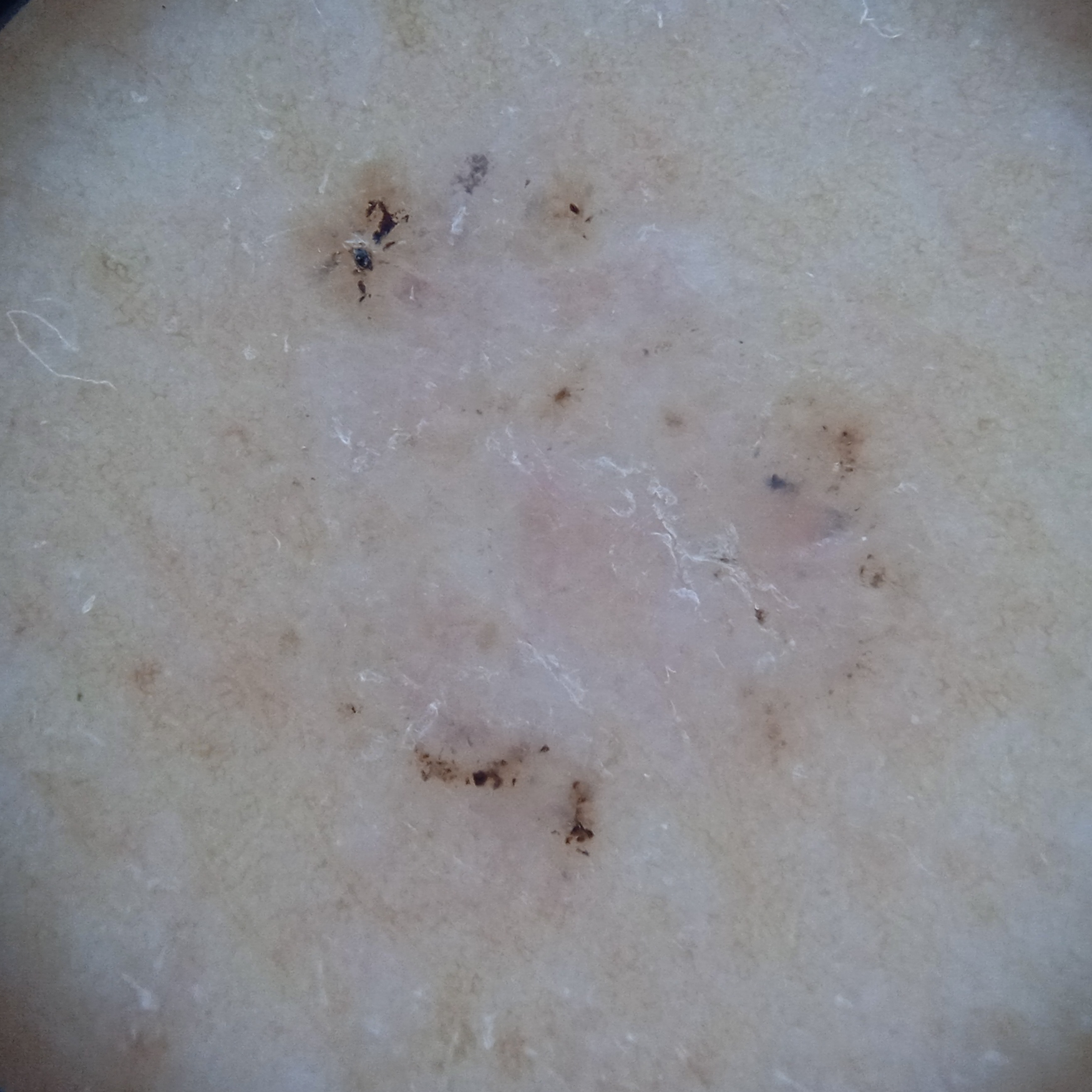{
  "mole_burden": "few melanocytic nevi overall",
  "patient": {
    "age": 60,
    "sex": "female"
  },
  "referral": "clinical suspicion of basal cell carcinoma",
  "risk_factors": {
    "positive": [
      "a personal history of skin cancer",
      "a personal history of cancer"
    ],
    "negative": [
      "no family history of skin cancer",
      "no immunosuppression"
    ]
  },
  "lesion_size": {
    "diameter_mm": 7.8
  },
  "diagnosis": {
    "name": "basal cell carcinoma",
    "malignancy": "malignant"
  }
}